A subject 81 years of age; a clinical photograph showing a skin lesion:
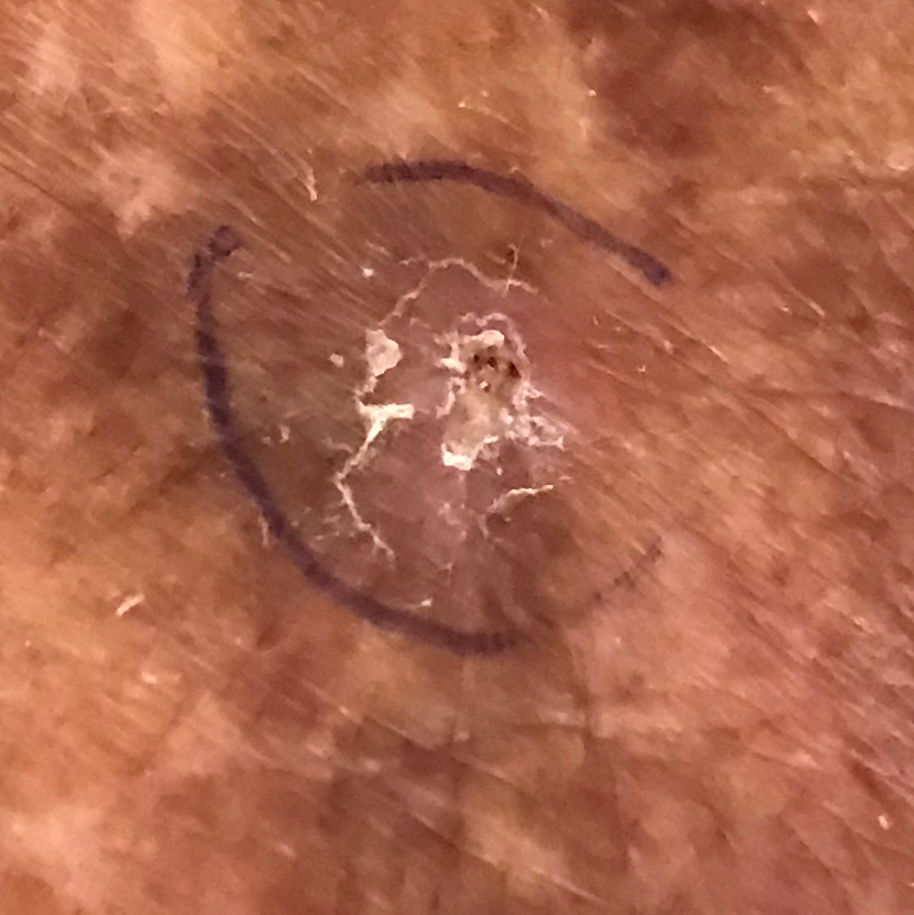– anatomic site: a forearm
– diagnosis: actinic keratosis (clinical consensus)